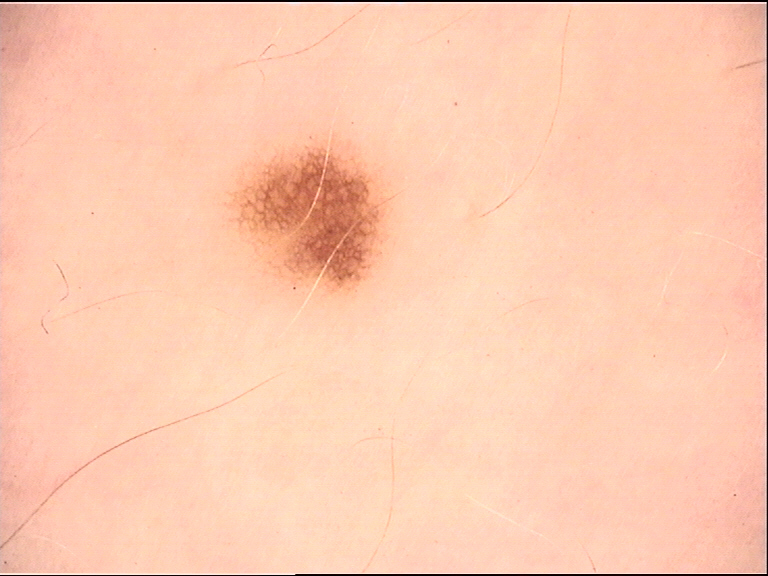A dermoscopic photograph of a skin lesion.
This is a banal lesion.
Labeled as a junctional nevus.